A dermoscopy image of a single skin lesion:
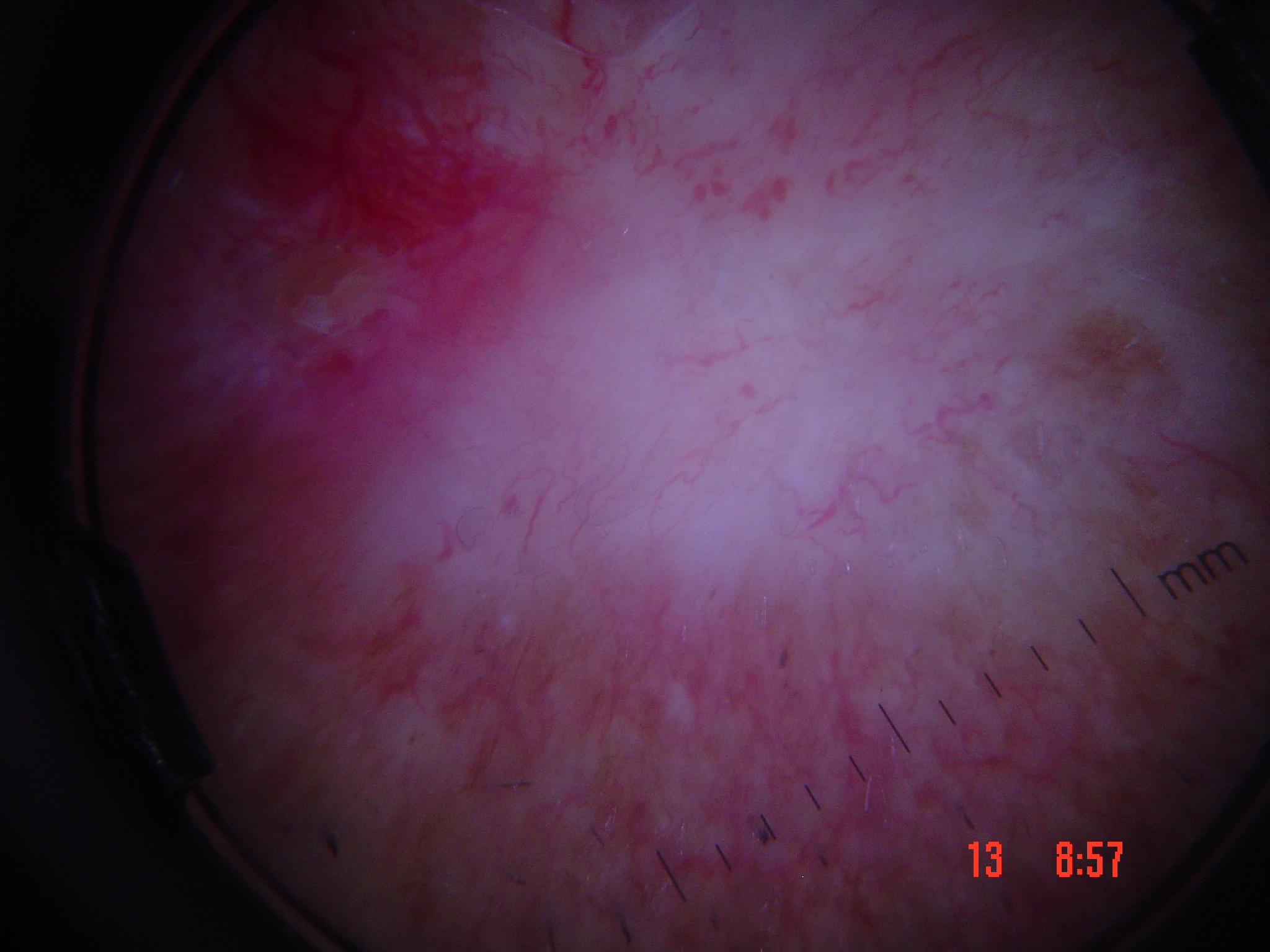Summary:
This is a keratinocytic lesion.
Diagnosis:
Histopathology confirmed a malignancy — a basal cell carcinoma.